Skin tone: lay reviewers estimated a Monk Skin Tone of 3. The patient notes the condition has been present for one to four weeks. The patient notes the lesion is raised or bumpy. An image taken at a distance:
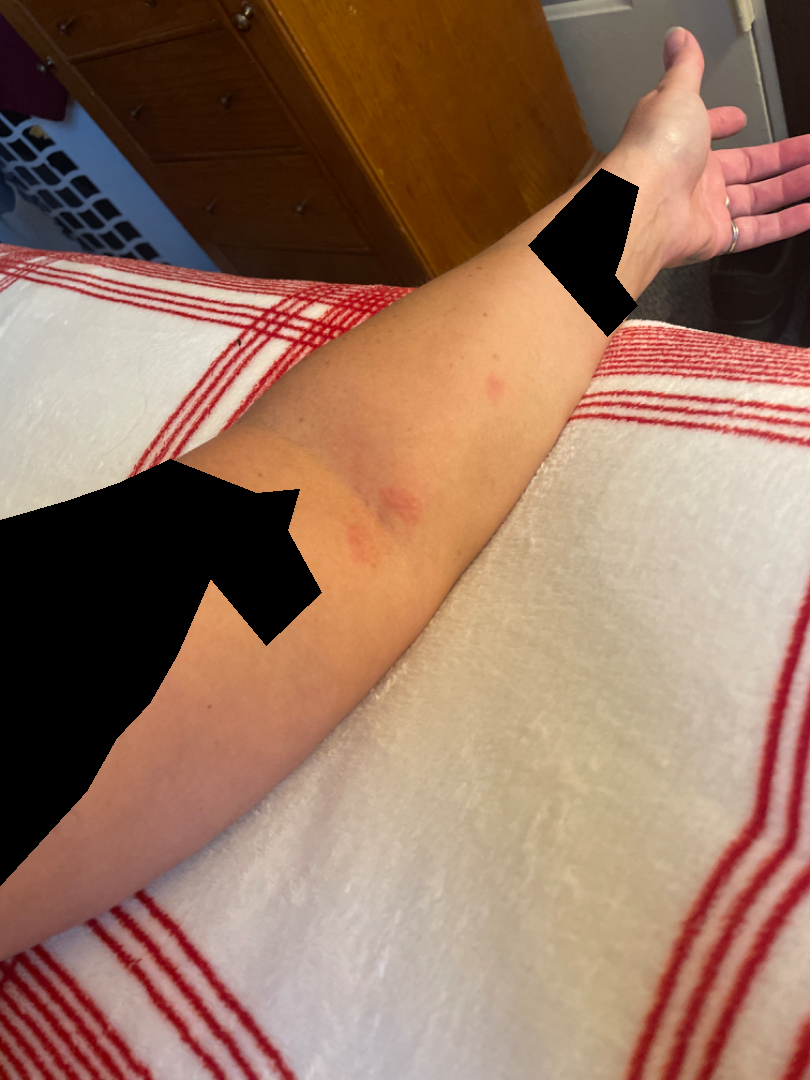Most consistent with Eczema.